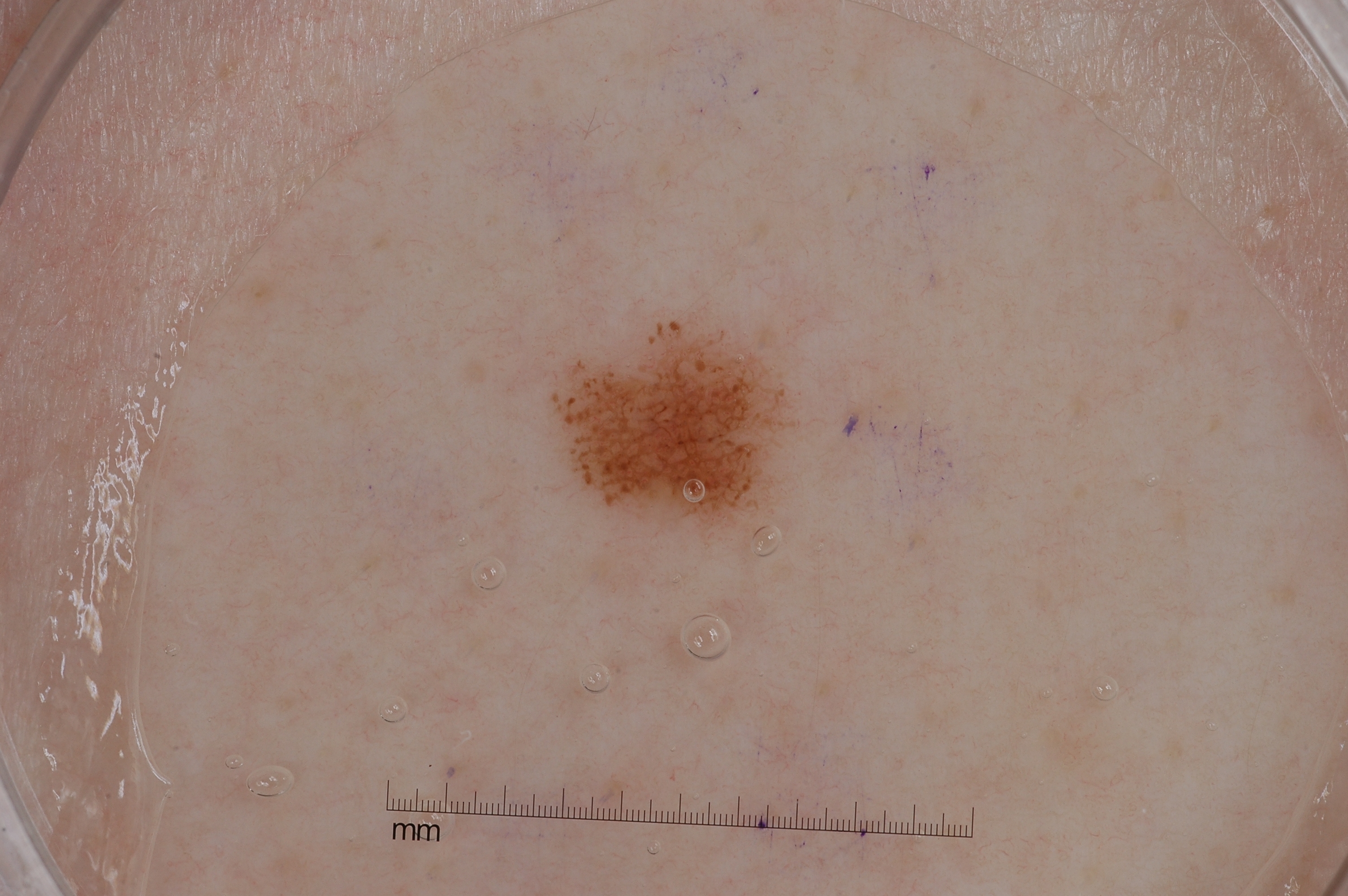Case summary:
A dermoscopy image of a single skin lesion. The lesion covers approximately 3% of the dermoscopic field. The lesion occupies the region x1=549 y1=319 x2=795 y2=537. Dermoscopy demonstrates pigment network.
Conclusion:
The clinical diagnosis was a melanocytic nevus, a benign lesion.